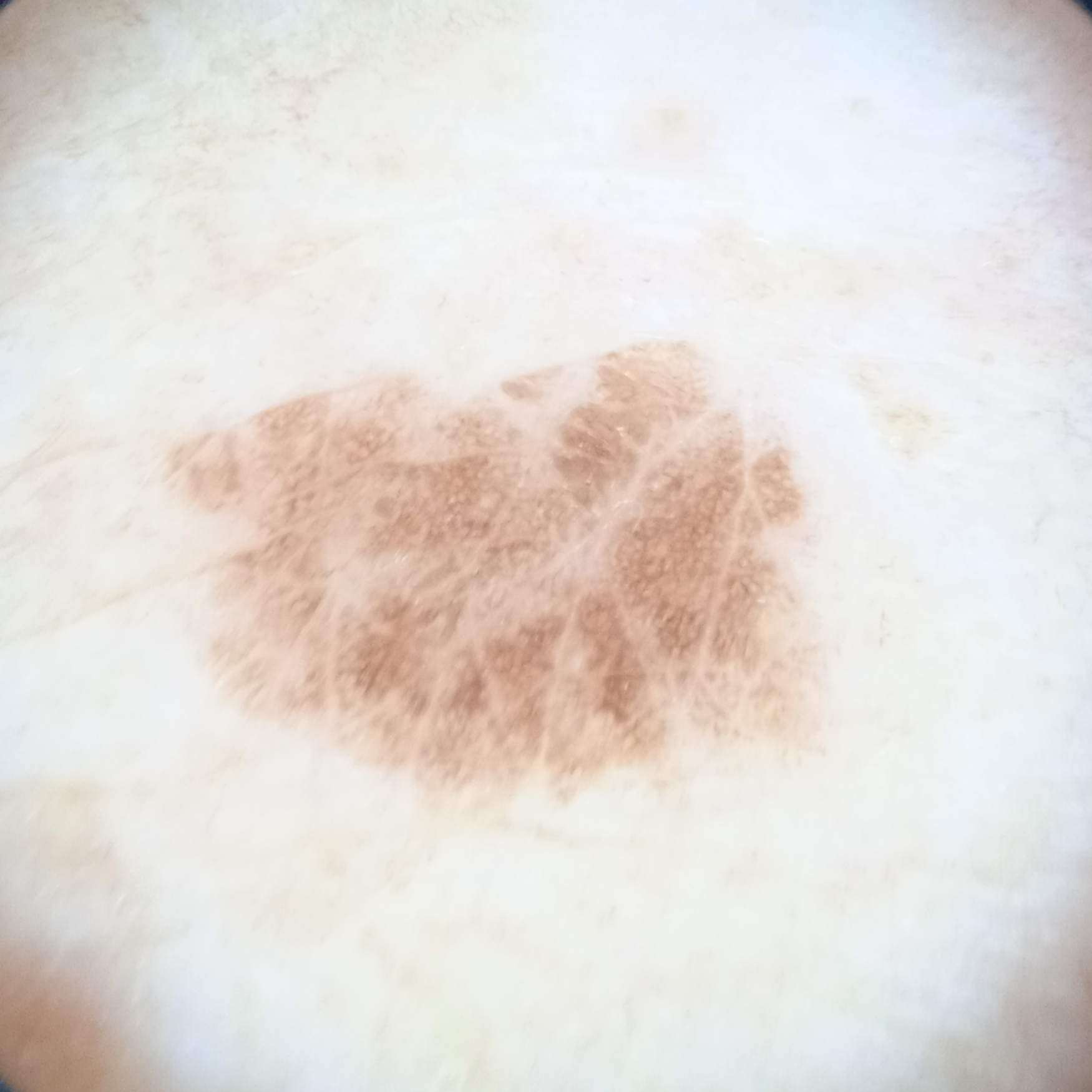Imaged for a research study, with no referral diagnosis recorded.
The lesion measures approximately 7.1 mm.
Four dermatologists reviewed the lesion; the consensus was a seborrheic keratosis; there was some disagreement among the reviewers; the reviewers were moderately confident.